The lesion involves the arm. The photo was captured at a distance. No associated lesion symptoms were reported. Female contributor, age 50–59. No relevant systemic symptoms. The patient notes the lesion is raised or bumpy. Fitzpatrick skin type IV. The condition has been present for less than one week — 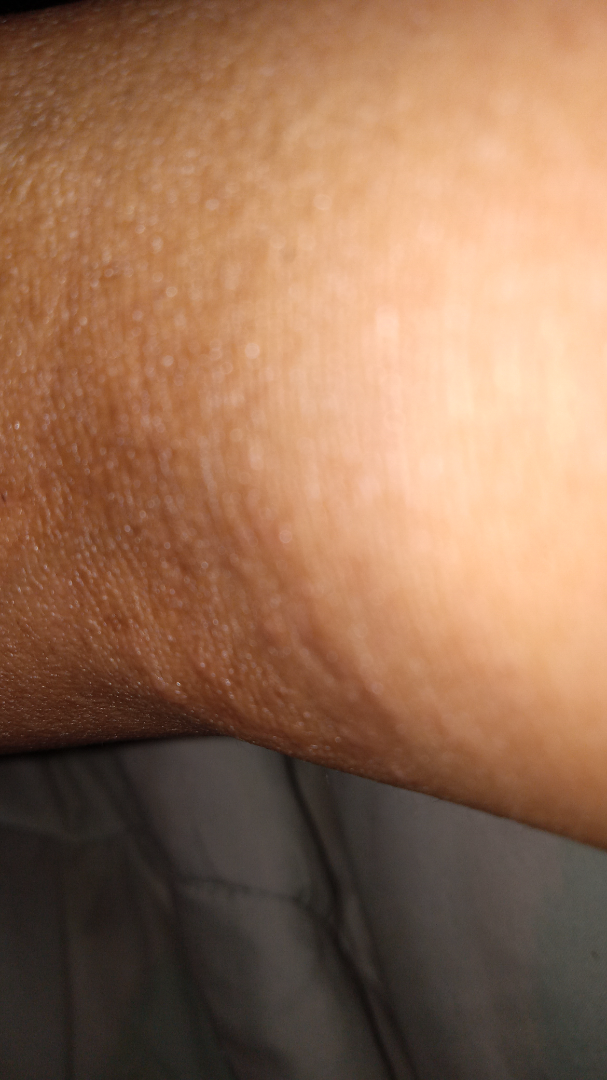Review:
The reviewer was unable to grade this case for skin condition.